A dermoscopic close-up of a skin lesion.
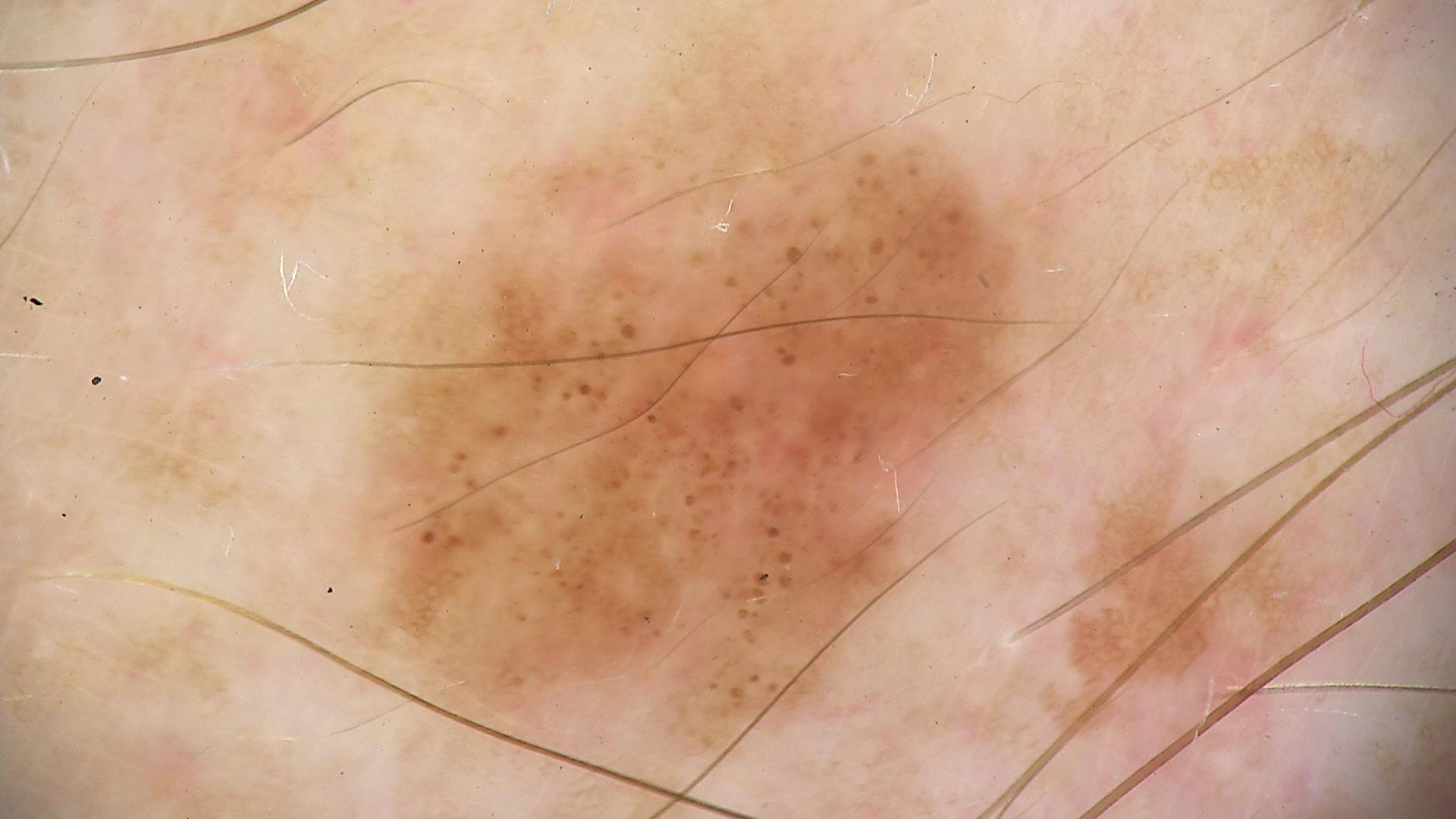Impression:
Classified as a dysplastic junctional nevus.